A skin lesion imaged with a dermatoscope.
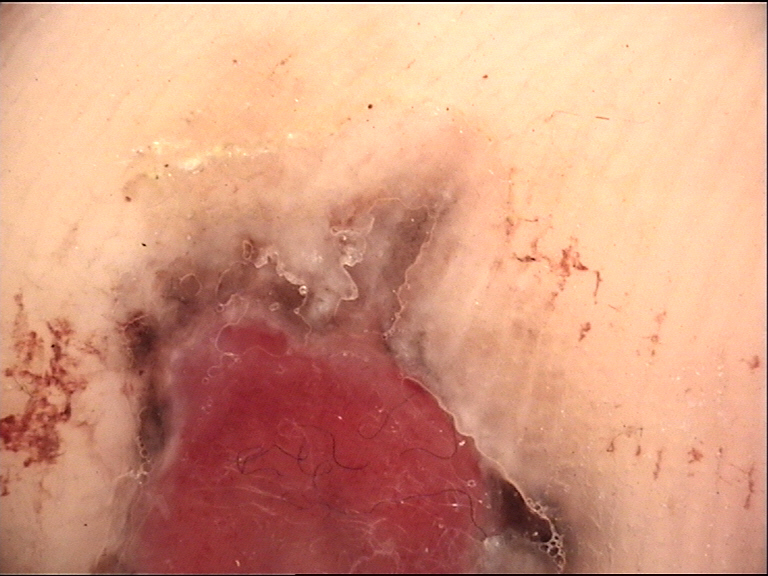diagnosis = acral nodular melanoma (biopsy-proven).